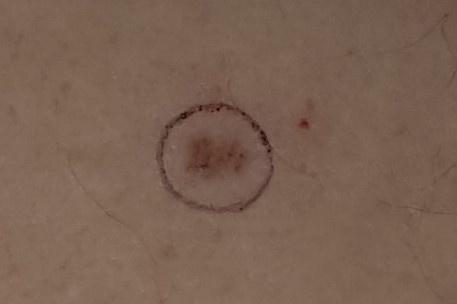Q: Patient demographics?
A: male, aged approximately 65
Q: Where is the lesion located?
A: the posterior trunk
Q: What did the workup show?
A: Basal cell carcinoma (biopsy-proven)